Dermoscopy of a skin lesion: 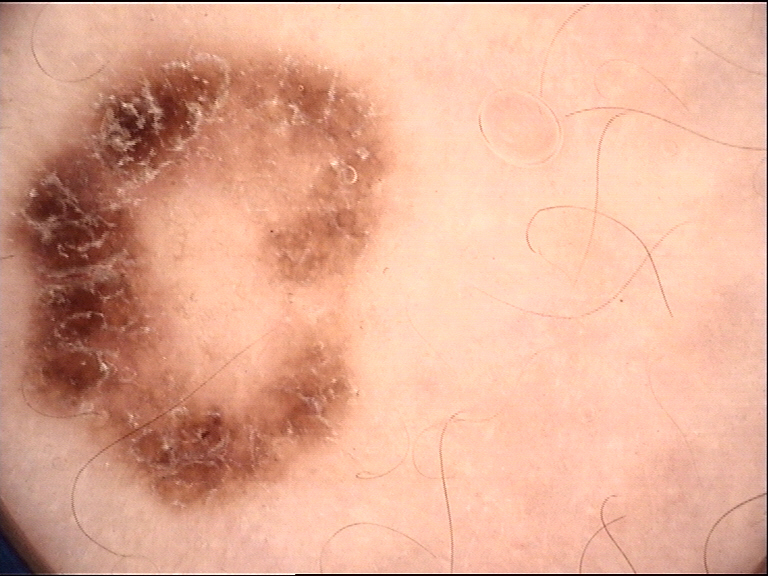The diagnosis was a keratinocytic, benign lesion — a seborrheic keratosis.